A close-up photograph: 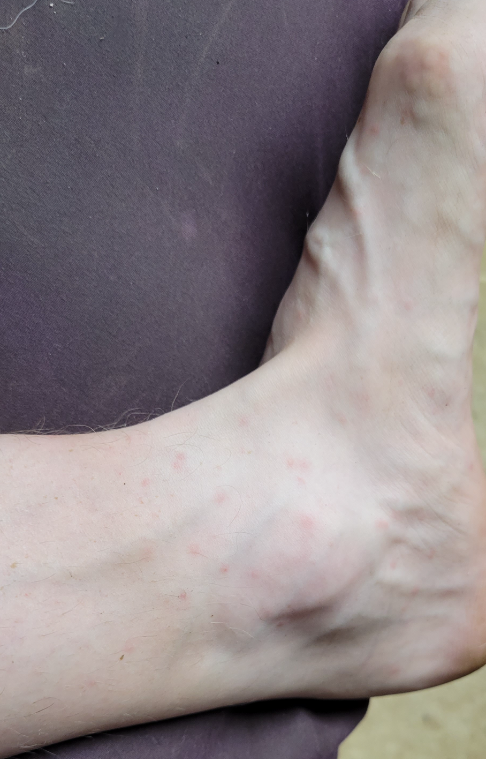On remote review of the image, Viral Exanthem, Folliculitis and Insect Bite were considered with similar weight.